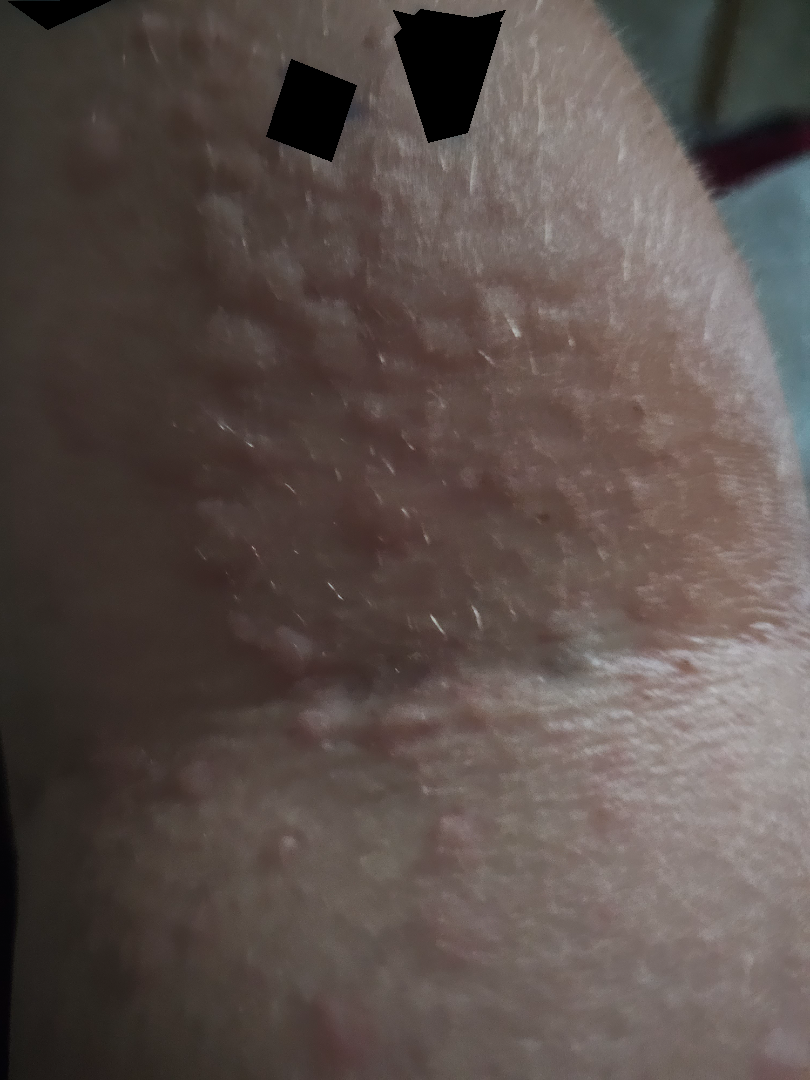Q: What is the framing?
A: close-up
Q: What conditions are considered?
A: consistent with Urticaria